The subject is a female about 75 years old. Dermoscopy of a skin lesion.
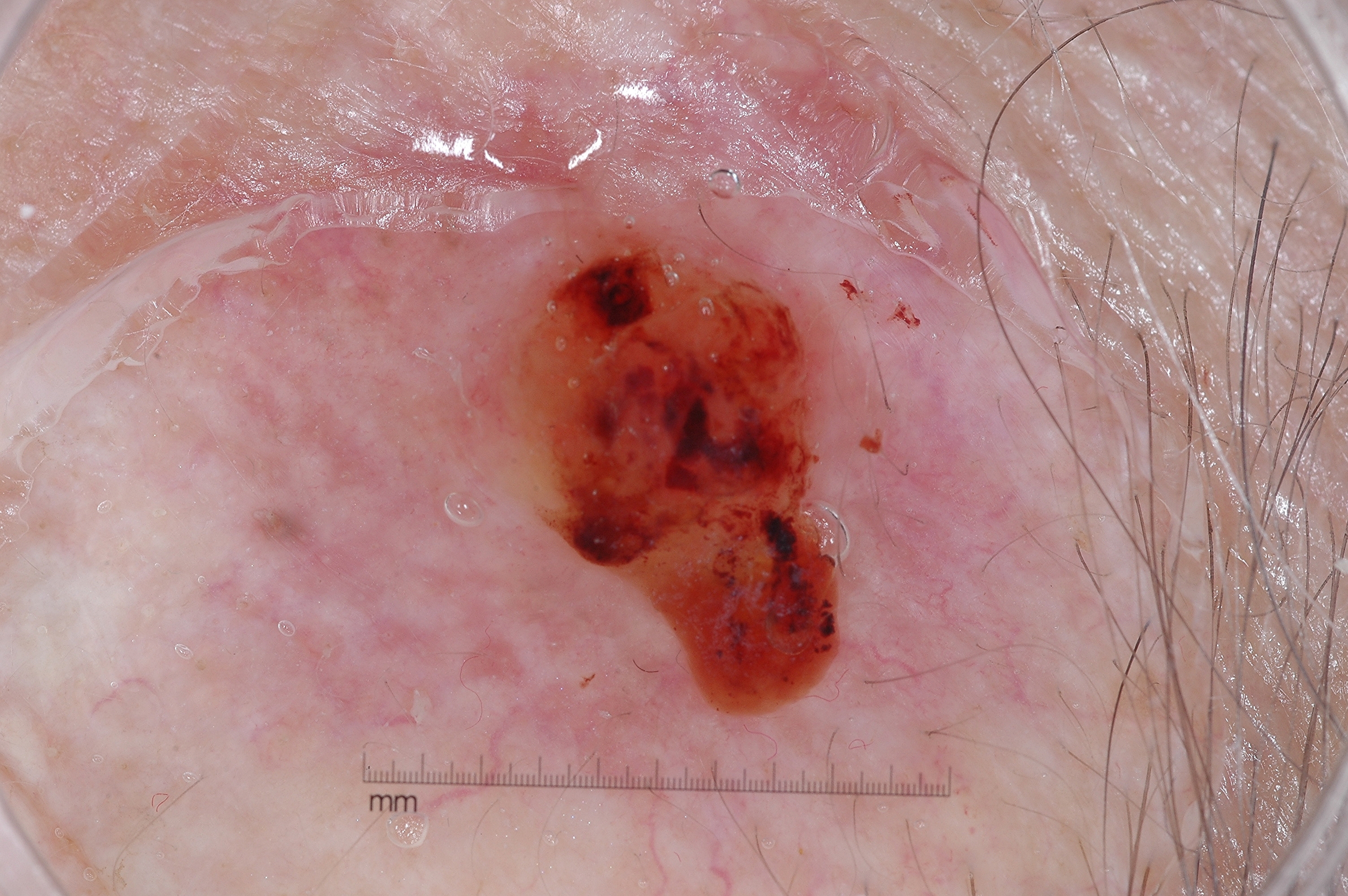Lesion location: box(137, 16, 1125, 879). The lesion covers approximately 60% of the dermoscopic field. Dermoscopic examination shows no pigment network, negative network, streaks, or milia-like cysts. Histopathologically confirmed as a melanoma.